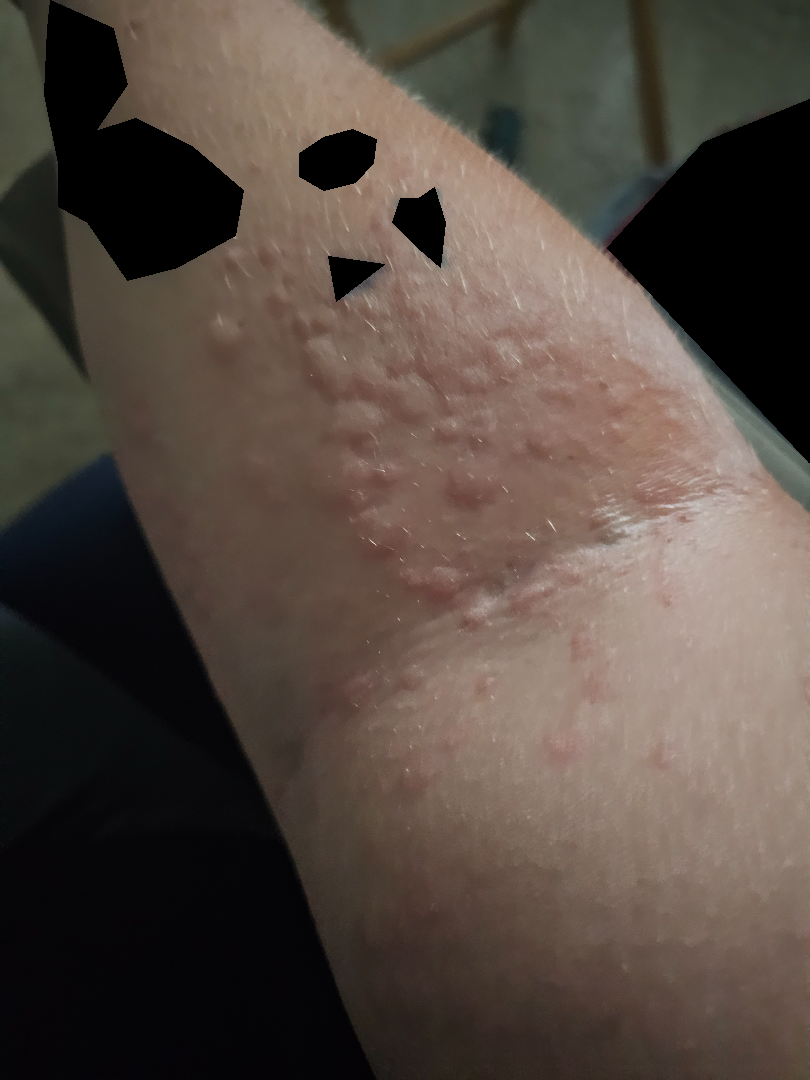Patient information:
This image was taken at an angle. Skin tone: Fitzpatrick phototype IV.
Review:
On photographic review by a dermatologist: the impression on review was Urticaria.